A dermoscopic close-up of a skin lesion.
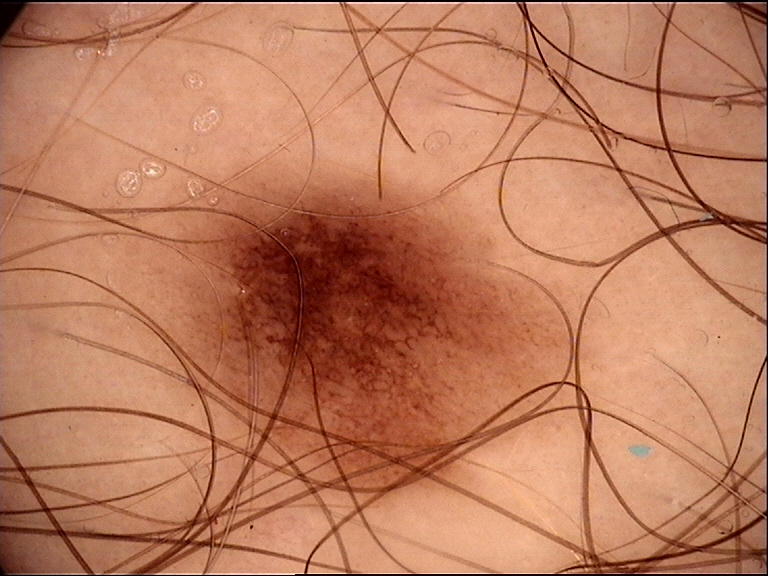Consistent with a dysplastic junctional nevus.